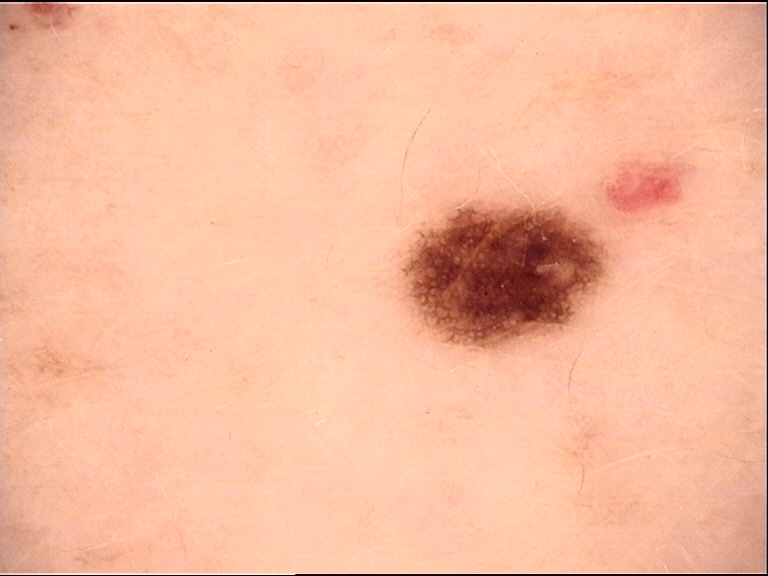image: dermoscopy
diagnosis:
  name: dysplastic junctional nevus
  code: jd
  malignancy: benign
  super_class: melanocytic
  confirmation: expert consensus